The patient is Fitzpatrick II · the chart notes a prior melanoma but no first-degree relative with melanoma · a male patient aged approximately 60:
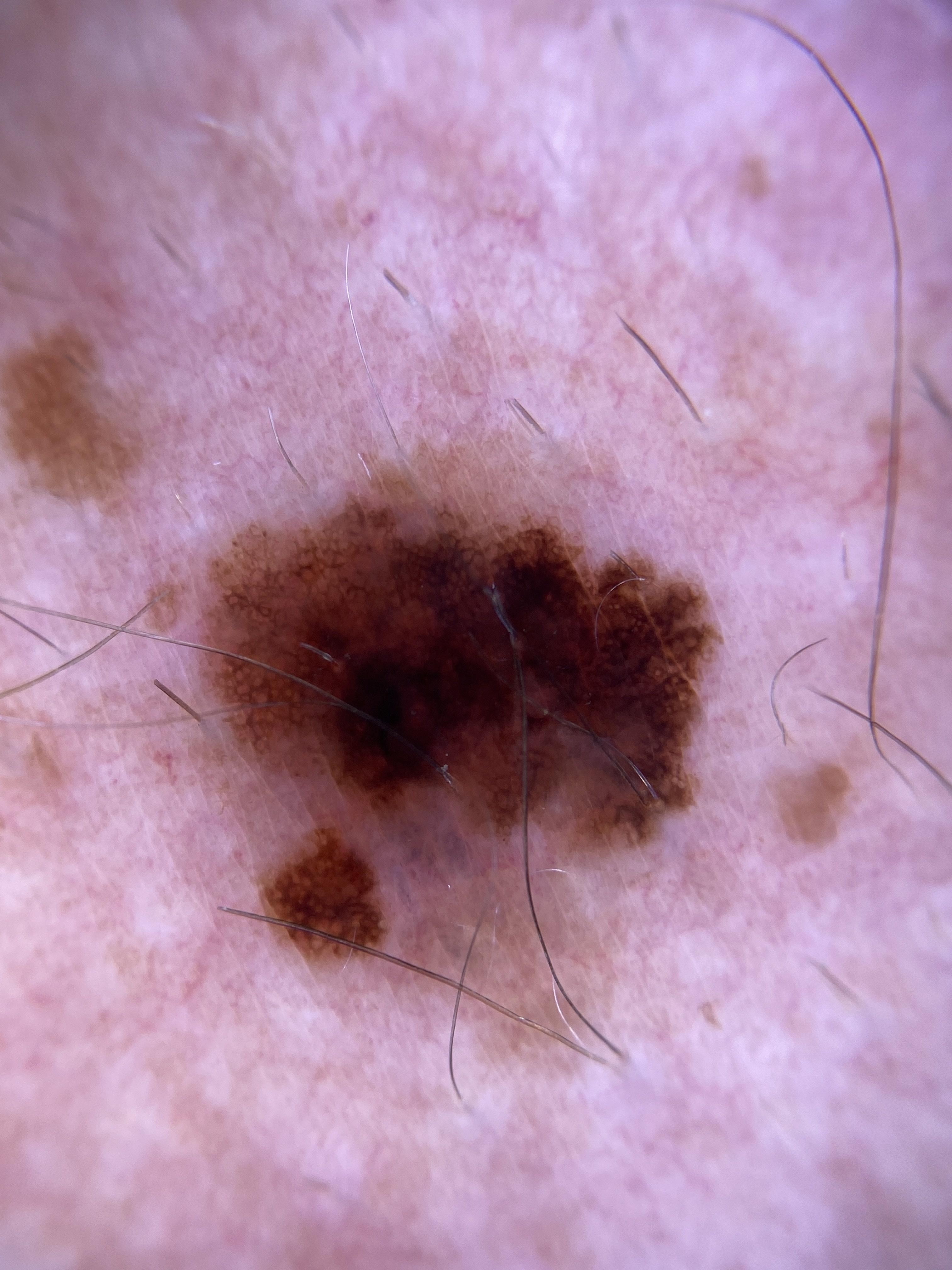The lesion was found on an upper extremity.
Histopathology confirmed a malignant lesion — a melanoma.